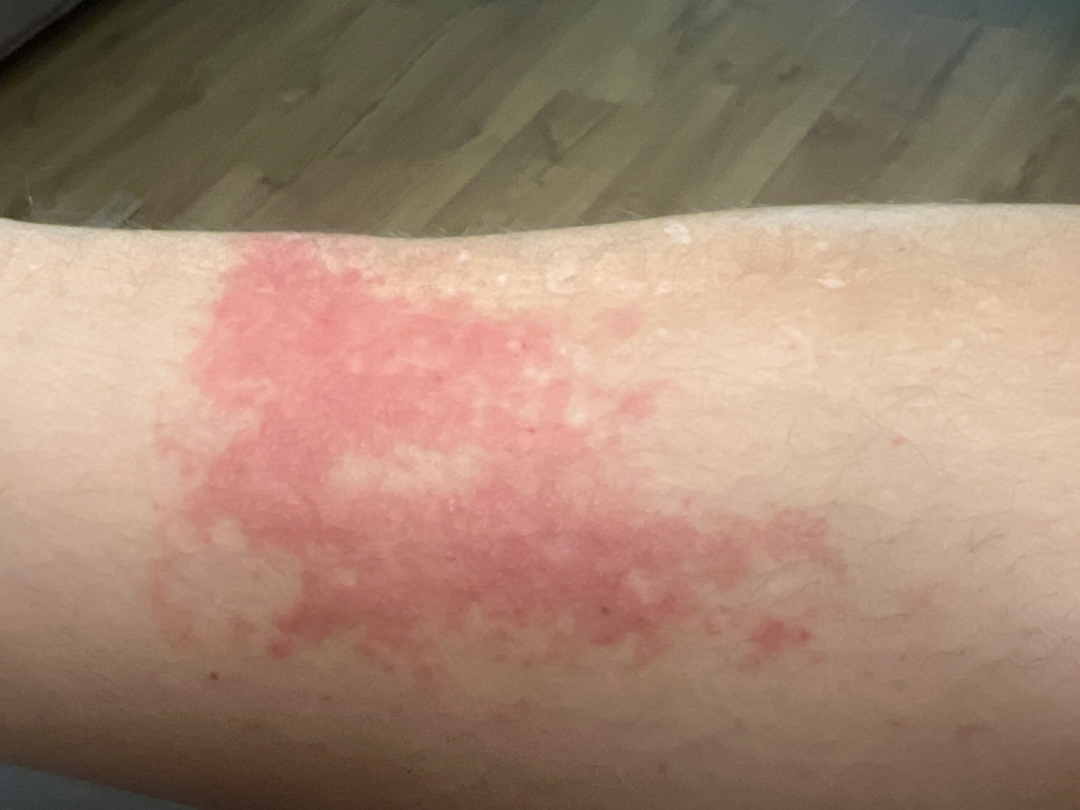Q: Who is the patient?
A: male, age 18–29
Q: Image view?
A: close-up
Q: What is the affected area?
A: leg
Q: What is the differential diagnosis?
A: Acute dermatitis, NOS (most likely)